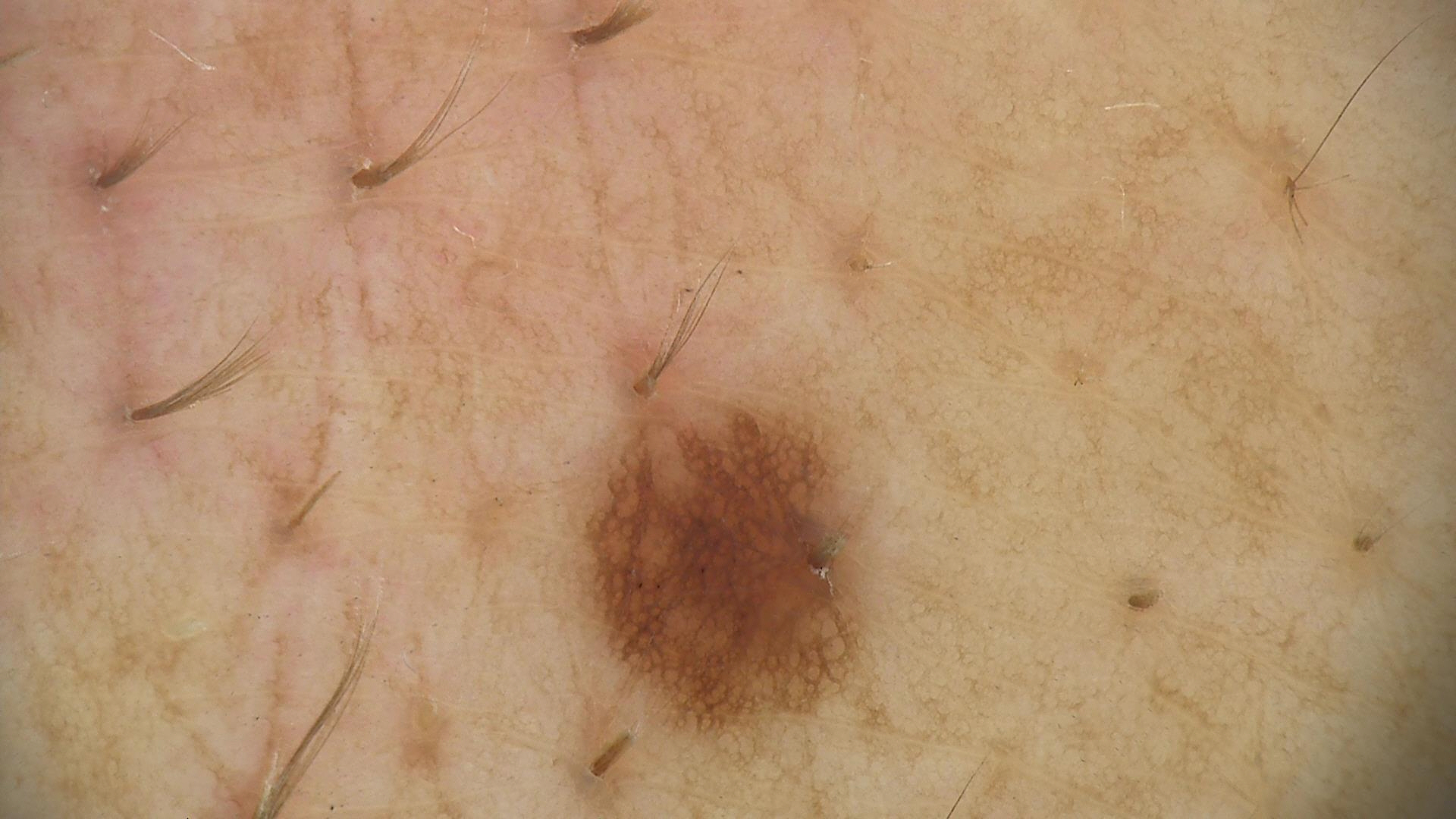A dermoscopic photograph of a skin lesion. Classified as a benign lesion — a dysplastic junctional nevus.